The affected area is the arm, this is a close-up image, the subject is male — 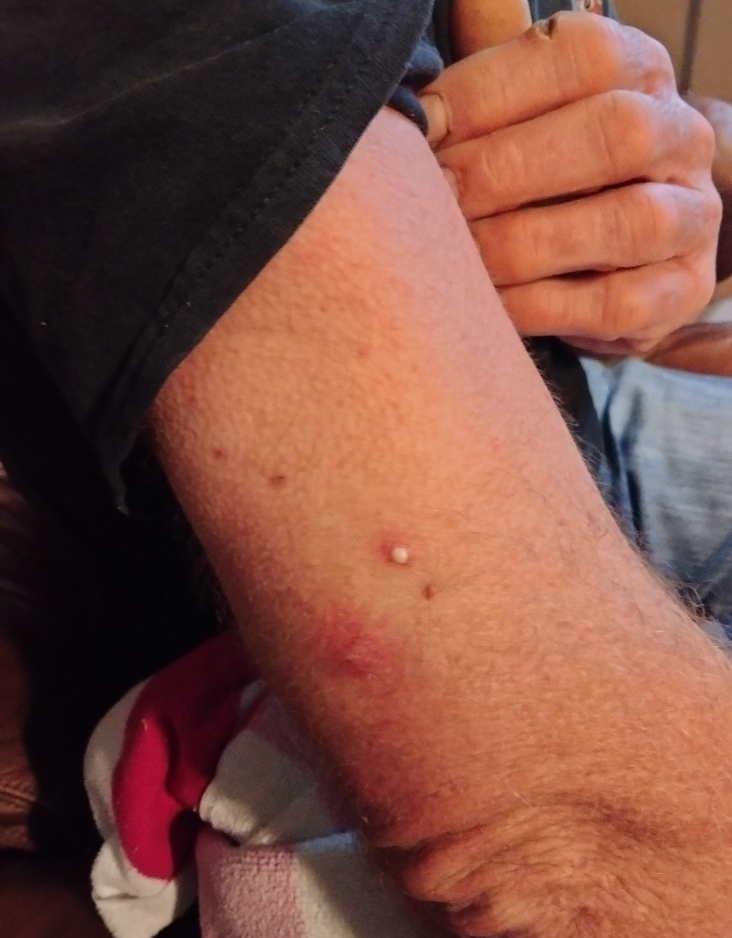Background:
The patient described the issue as skin that appeared healthy to them. The patient also reports fatigue. The patient indicates the condition has been present for one to four weeks. Texture is reported as raised or bumpy and fluid-filled.
Findings:
On remote dermatologist review: the impression on review was pustules.